The patient reports a personal history of cancer, no family history of skin cancer, and no immunosuppression · the patient says their skin tans without first burning · a dermoscopy image of a skin lesion · acquired for a research image collection, with no referral diagnosis · a female subject 84 years old:
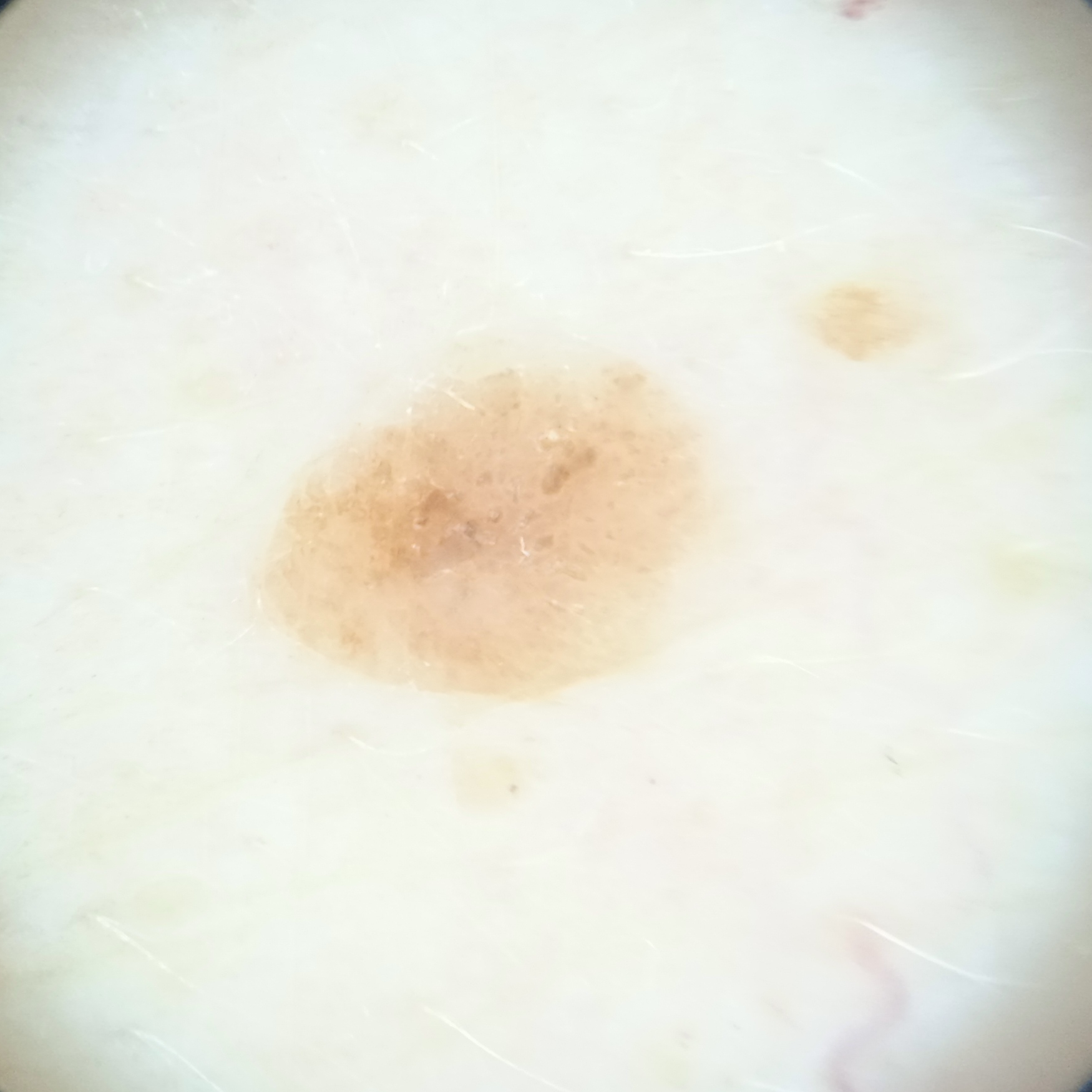site=the torso | diameter=5.9 mm | assessment=seborrheic keratosis (dermatologist consensus).